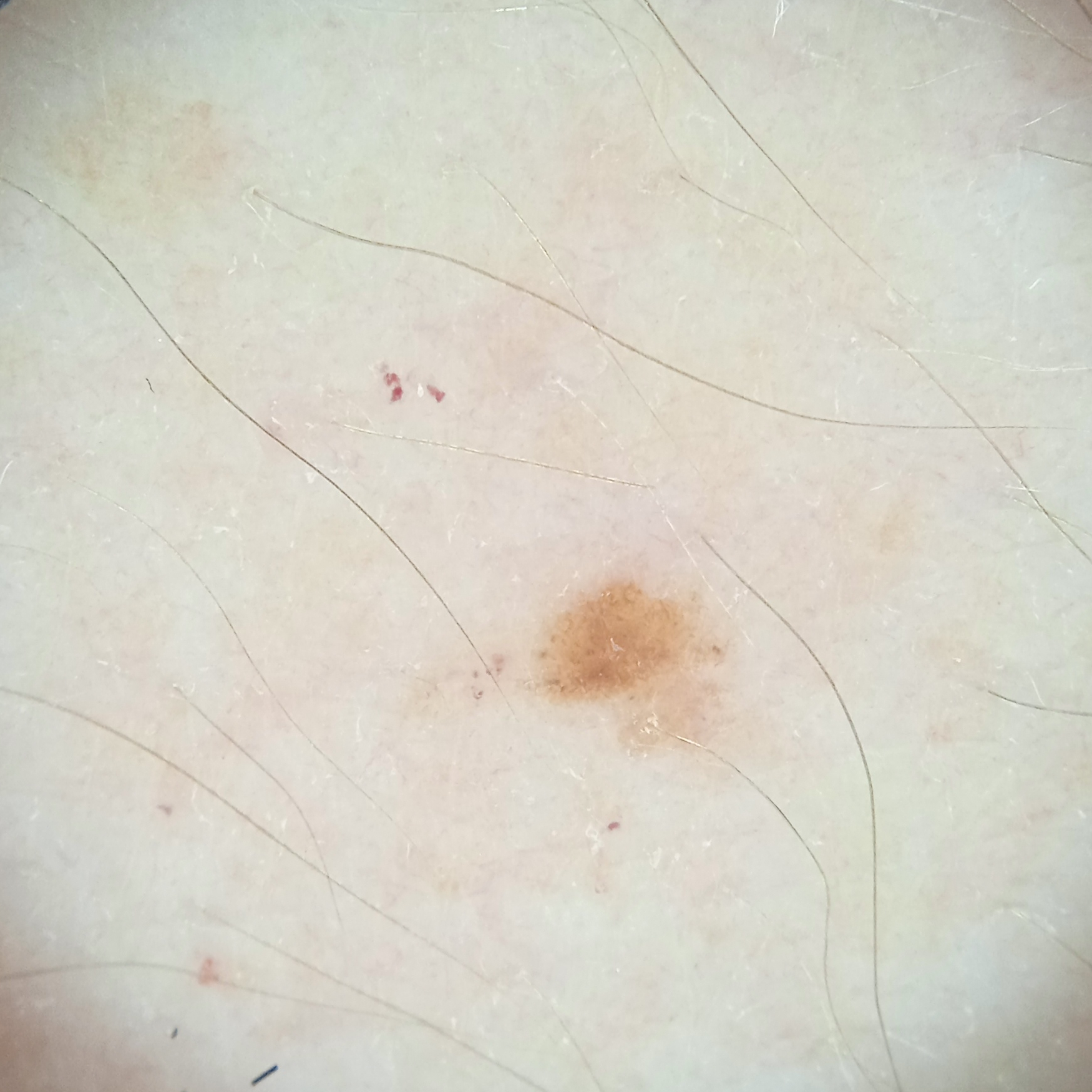subject — female, age 35; sun reaction — skin reddens painfully with sun exposure; nevus count — a moderate number of melanocytic nevi; clinical context — research study (no referral diagnosis); modality — dermatoscopic image; location — an arm; lesion size — 2.1 mm; diagnostic label — melanocytic nevus (dermatologist consensus).